Imaged for a research study, with no referral diagnosis recorded; the patient says their skin tans without first burning; a male patient age 72: 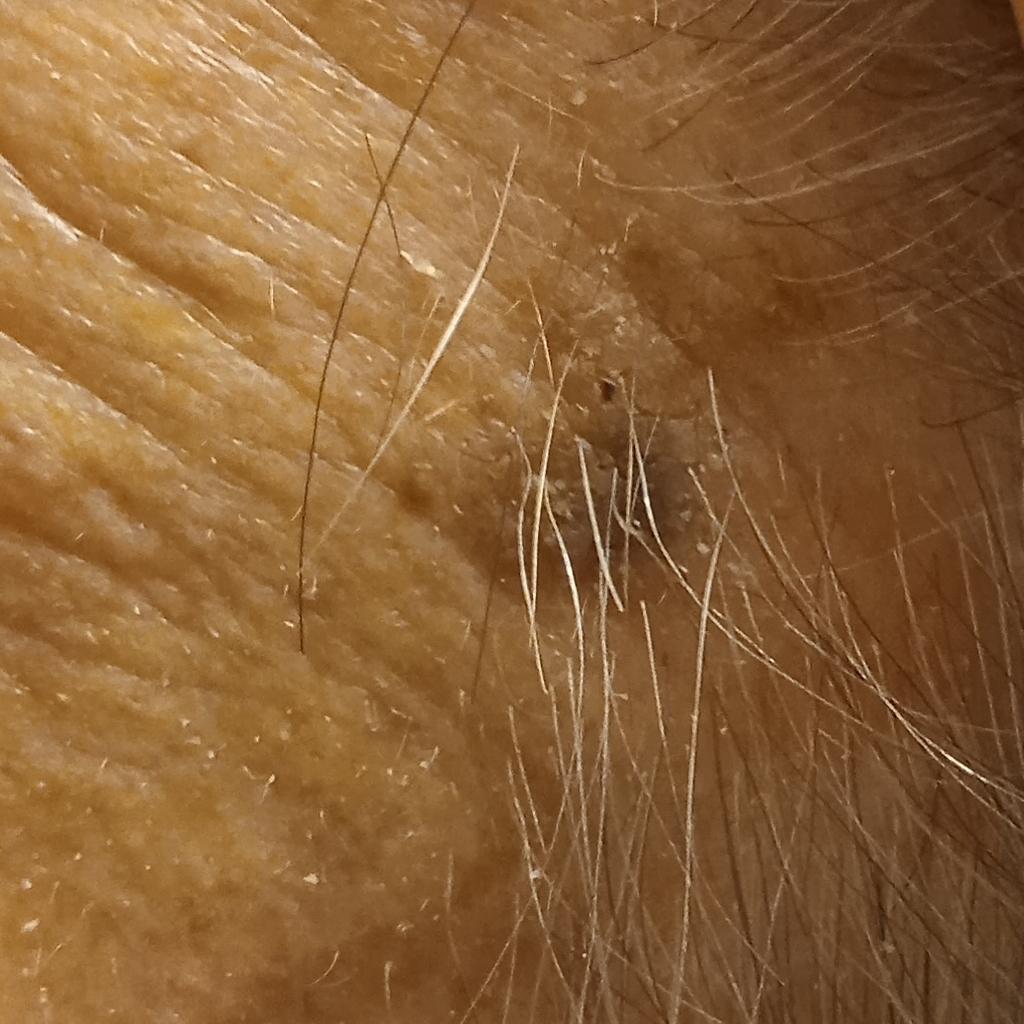The lesion involves an arm. The lesion measures approximately 7.3 mm. The diagnostic impression was a seborrheic keratosis.